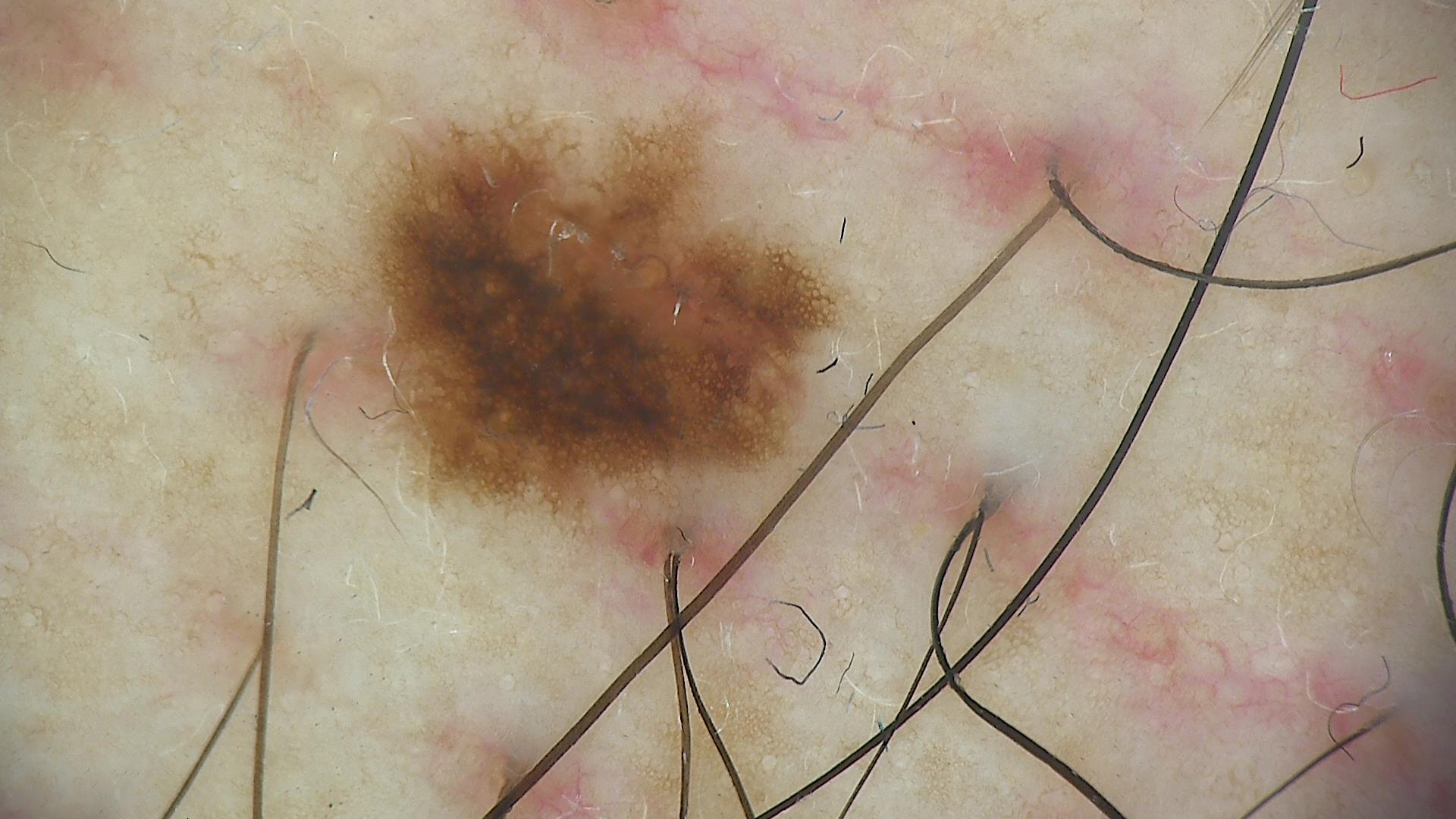imaging: dermatoscopy
assessment: dysplastic junctional nevus (expert consensus)